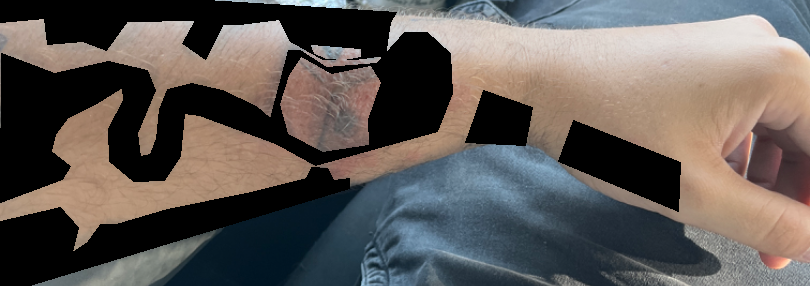Findings:
The dermatologist could not determine a likely condition from the photograph alone.